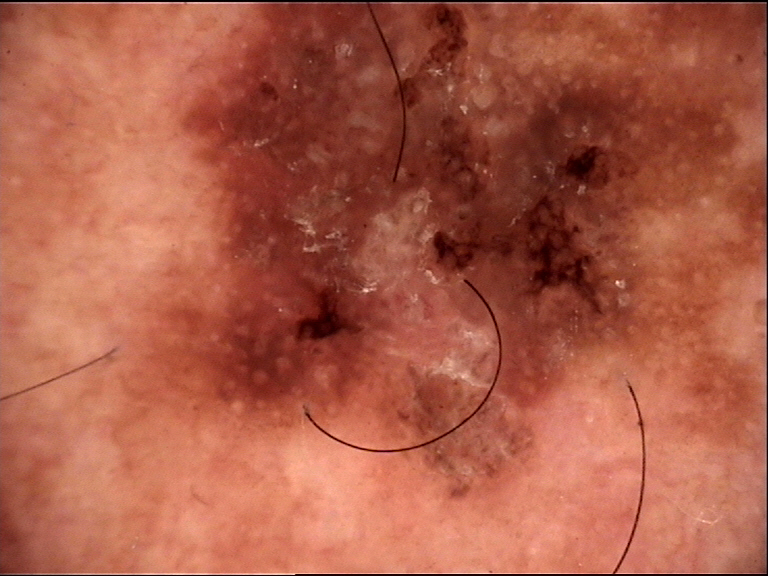  image: dermoscopy
  diagnosis:
    name: lentigo maligna
    code: lm
    malignancy: malignant
    super_class: melanocytic
    confirmation: histopathology